A smartphone photograph of a skin lesion.
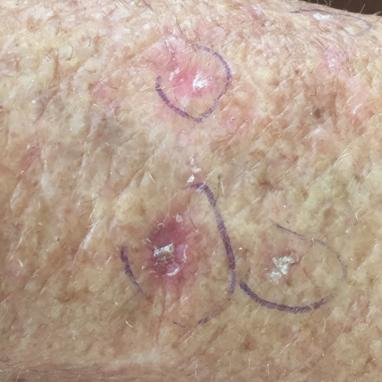The lesion was found on a forearm.
Per patient report, the lesion itches.
The diagnostic impression was an actinic keratosis.